A female patient approximately 25 years of age, a dermoscopic view of a skin lesion: 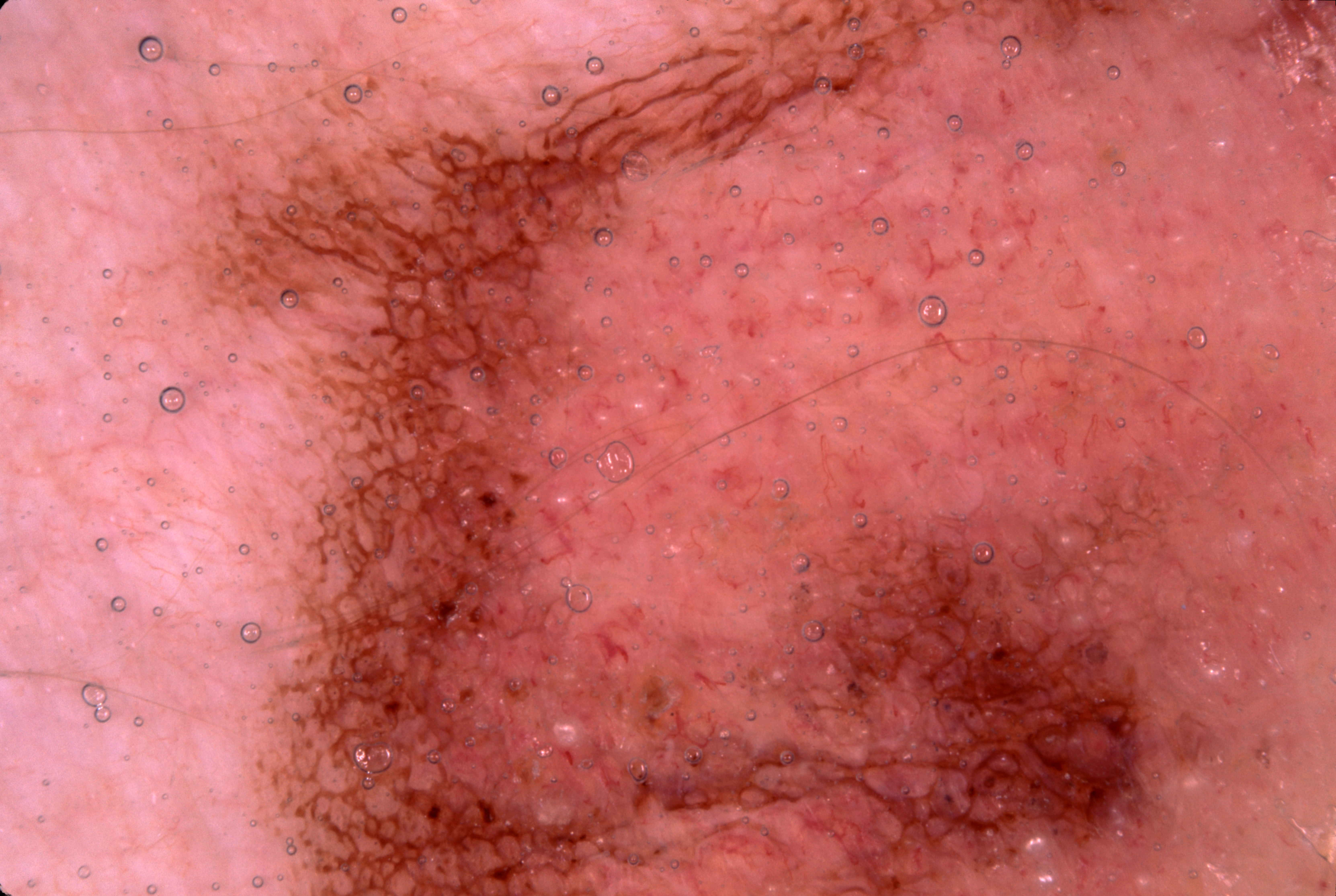Dermoscopic review identifies milia-like cysts and pigment network, with no negative network or streaks.
The lesion spans essentially the entire dermoscopic field.
The diagnostic assessment was a melanocytic nevus.